The patient described the issue as a rash · present for less than one week · an image taken at a distance · the contributor reports the lesion is raised or bumpy · skin tone: Fitzpatrick skin type III; human graders estimated Monk skin tone scale 2–3 · no constitutional symptoms were reported · the back of the torso, arm, leg and front of the torso are involved · the contributor reports itching and enlargement:
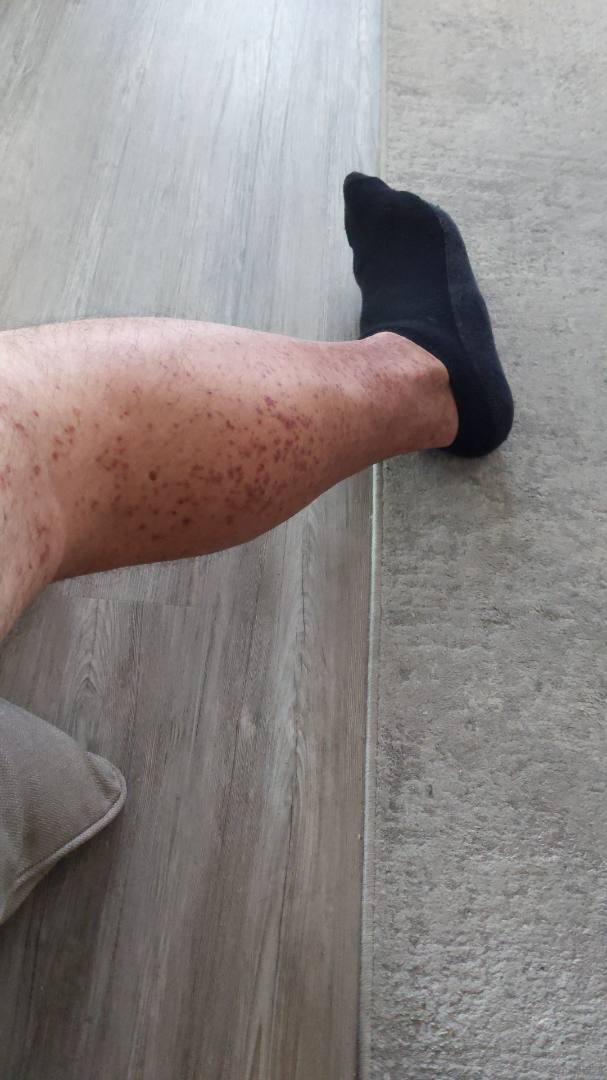On photographic review by a dermatologist: consistent with Leukocytoclastic Vasculitis.